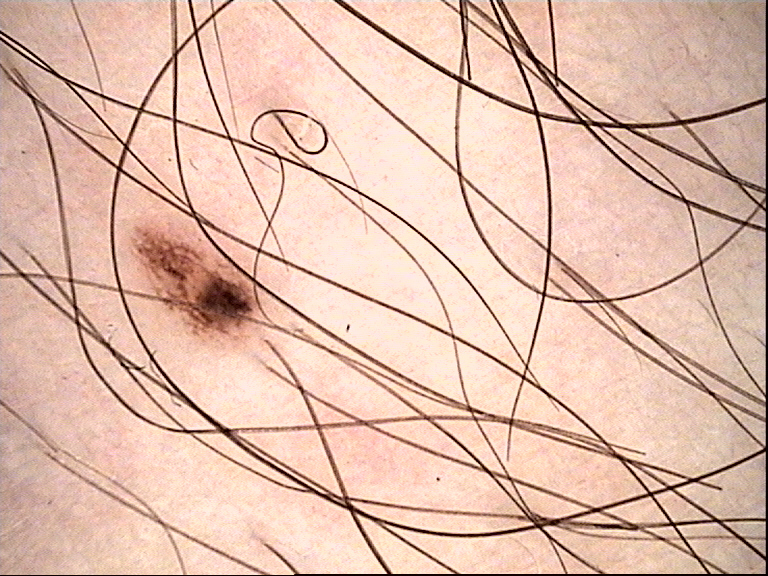A dermoscopic close-up of a skin lesion. Labeled as a benign lesion — a dysplastic junctional nevus.